A male subject in their mid-60s · the patient is Fitzpatrick phototype II · the chart notes tobacco use, pesticide exposure, alcohol use, no prior malignancy (patient or family), and no prior skin cancer (patient or family) · a clinical photo of a skin lesion taken with a smartphone: 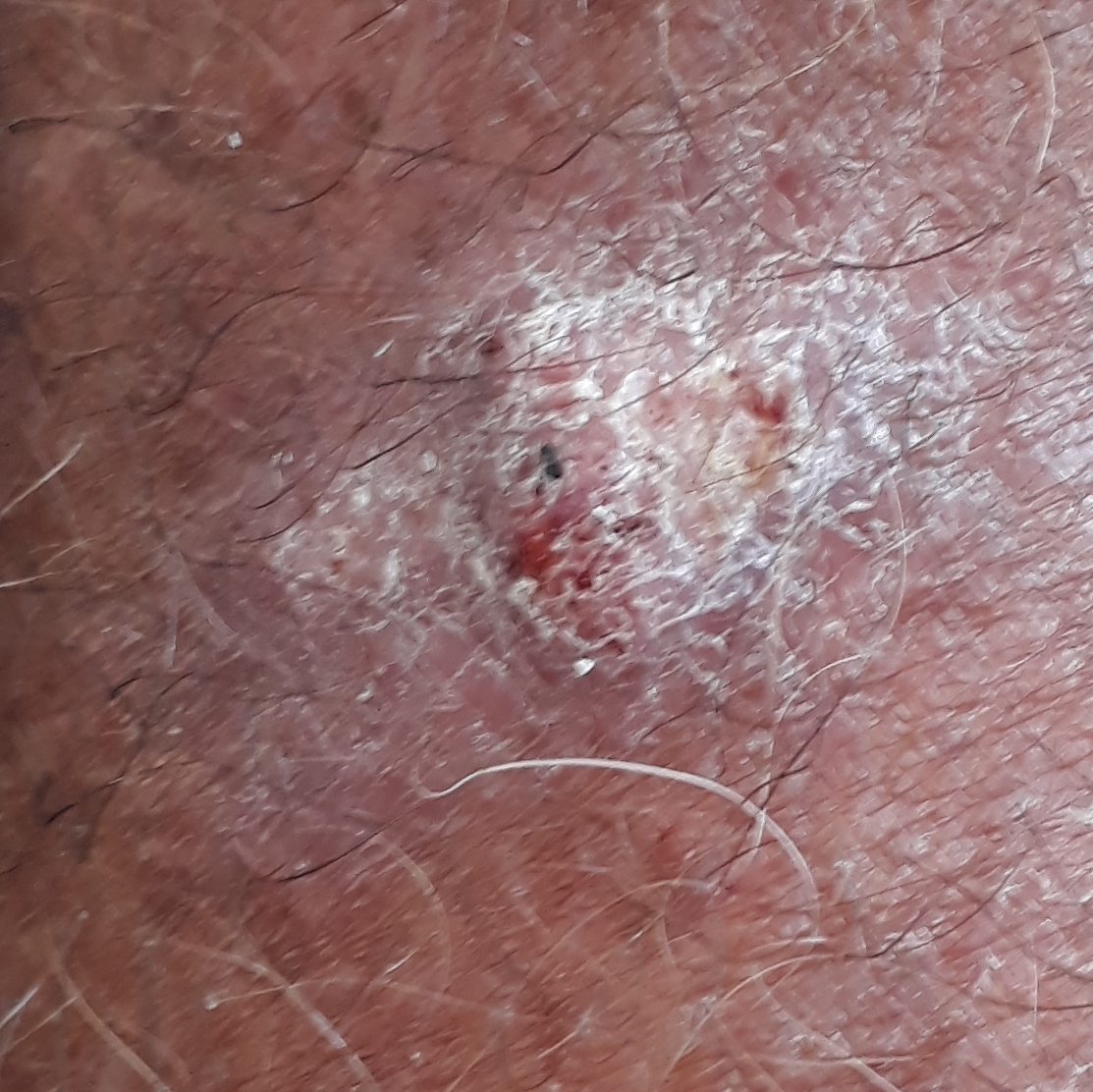The lesion is on a forearm. The lesion measures 15 × 13 mm. Biopsy-confirmed as a squamous cell carcinoma.